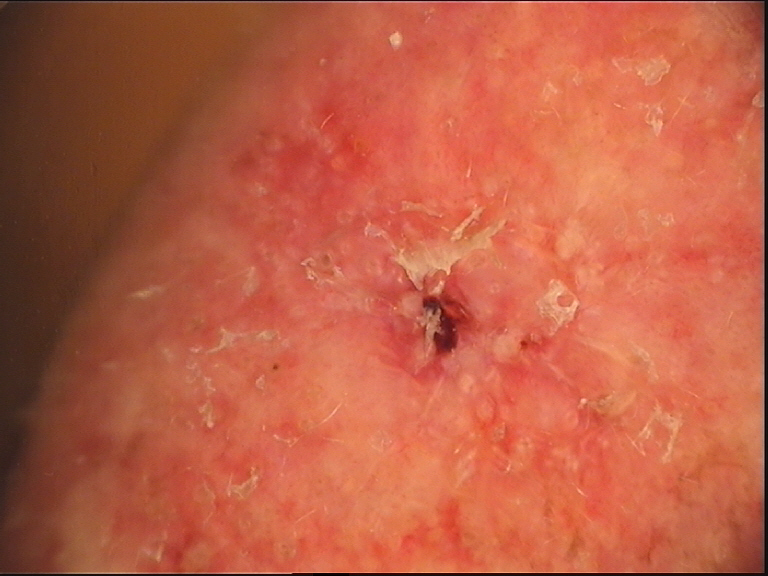label — basal cell carcinoma (biopsy-proven)